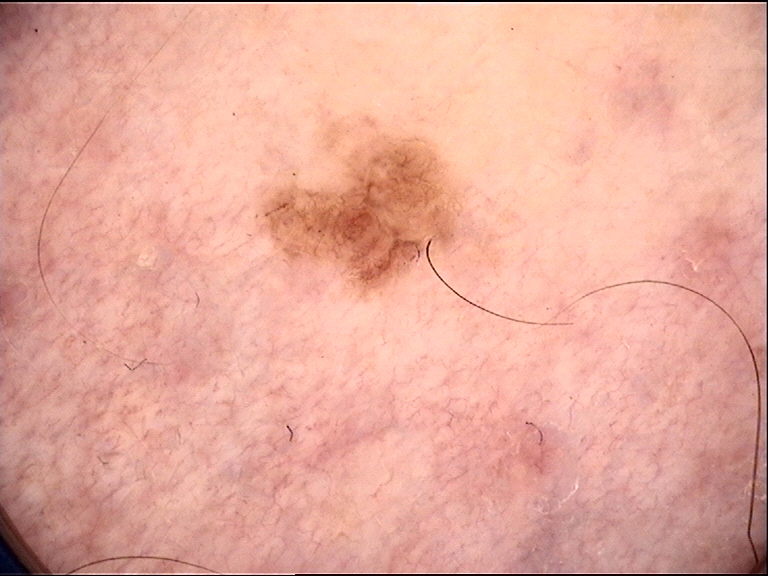Impression:
Classified as a benign lesion — a dysplastic junctional nevus.